A dermoscopic photograph of a skin lesion.
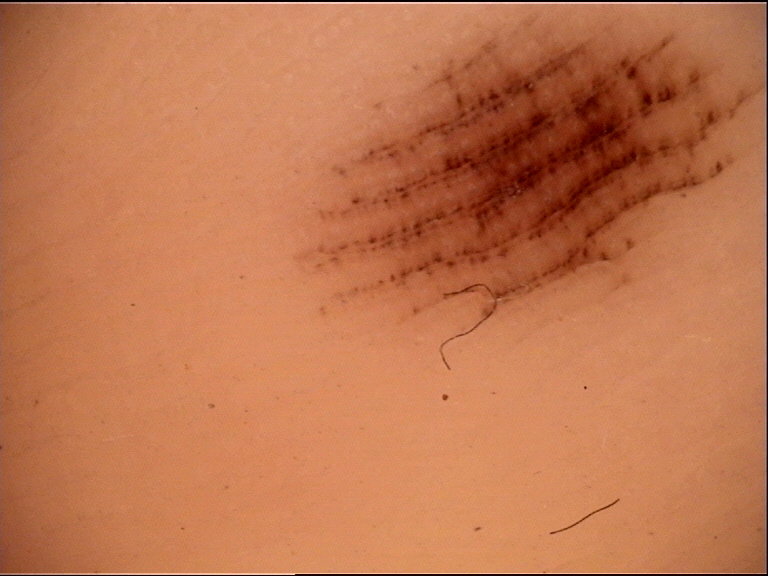This is a banal lesion.
The diagnosis was an acral junctional nevus.